Dermoscopy of a skin lesion · a female patient, roughly 40 years of age — 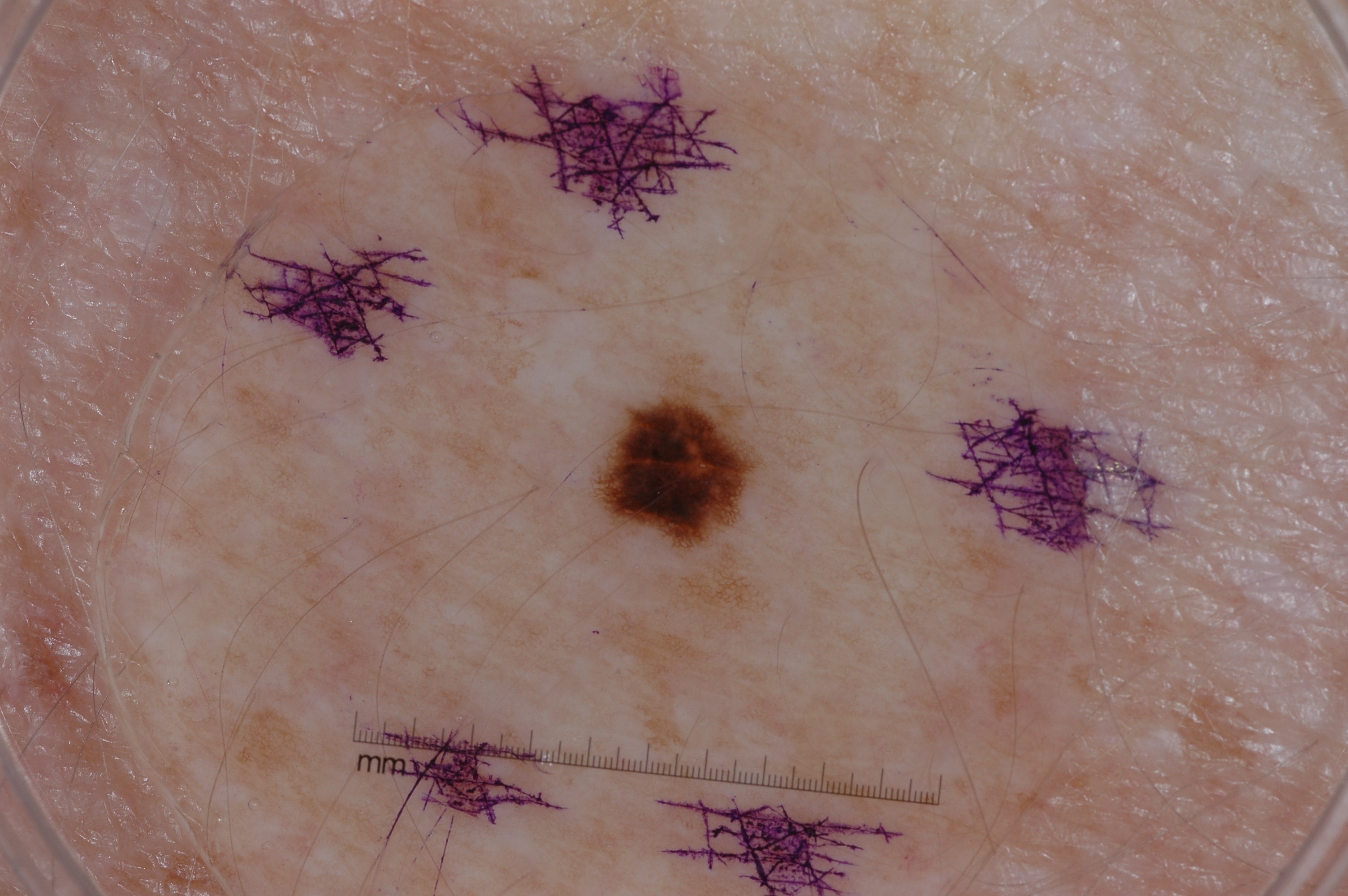As (left, top, right, bottom), the lesion is bounded by (611, 392, 747, 532).
The dermoscopic pattern shows pigment network.
Diagnosed as a melanocytic nevus.